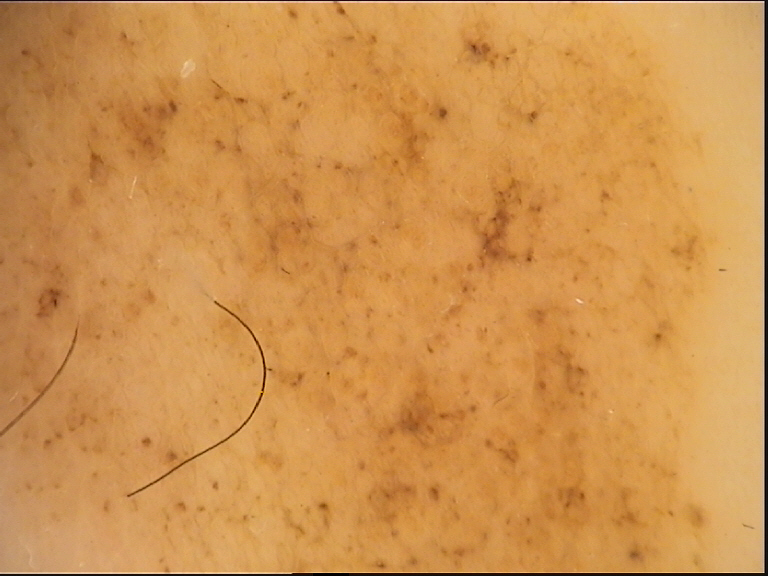{"diagnosis": {"name": "congenital junctional nevus", "code": "cjb", "malignancy": "benign", "super_class": "melanocytic", "confirmation": "expert consensus"}}